Close-up view, located on the arm — 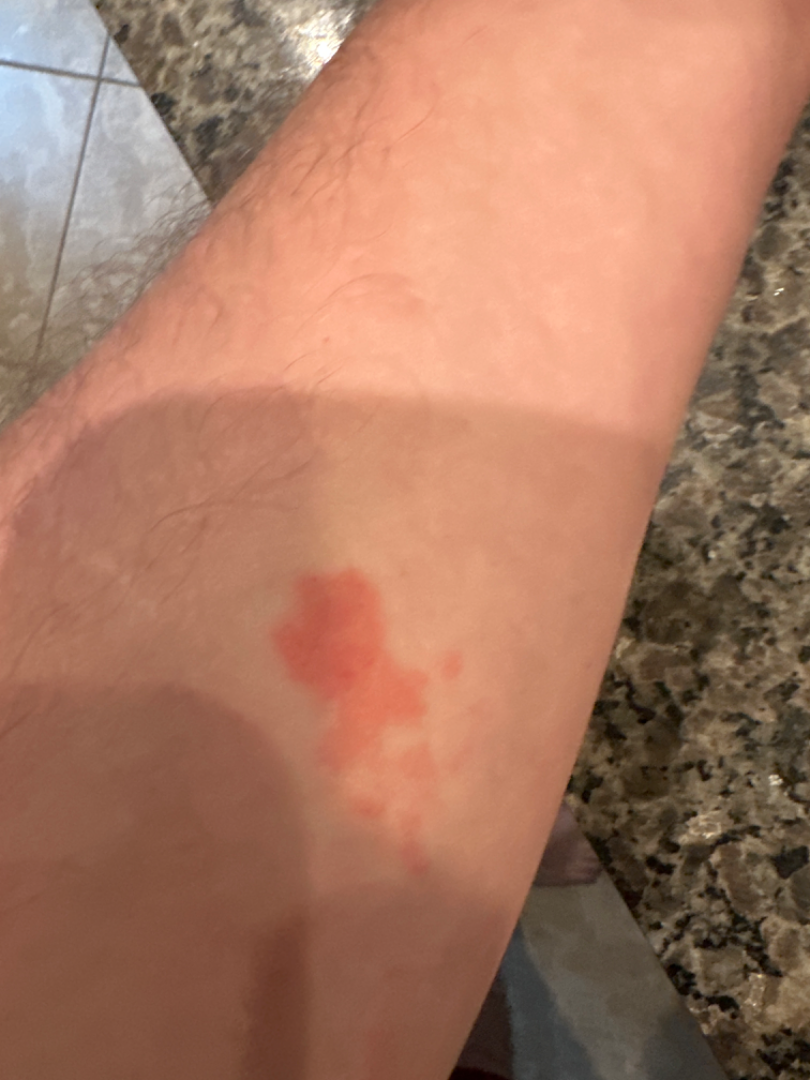self-categorized as: a rash | surface texture: raised or bumpy | other reported symptoms: none reported | duration: less than one week | dermatologist impression: most consistent with Urticaria; also consider Insect Bite.